The lesion is described as raised or bumpy; reported duration is less than one week; the patient considered this skin that appeared healthy to them; an image taken at an angle; the leg is involved; skin tone: human graders estimated MST 2 — 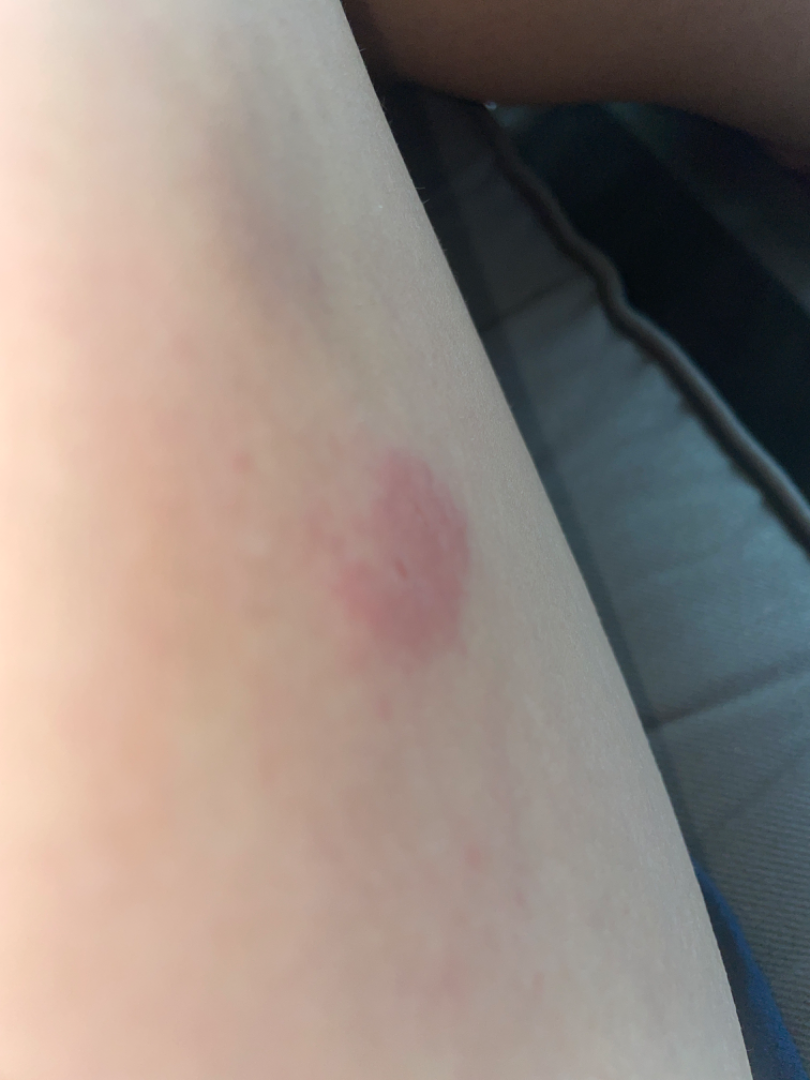Findings:
The reviewing dermatologist was unable to assign a differential diagnosis from the image.